The lesion is associated with bothersome appearance · self-reported Fitzpatrick phototype II · the palm is involved · the patient notes the lesion is raised or bumpy · the photograph was taken at an angle · reported duration is less than one week · the contributor is a female aged 50–59.
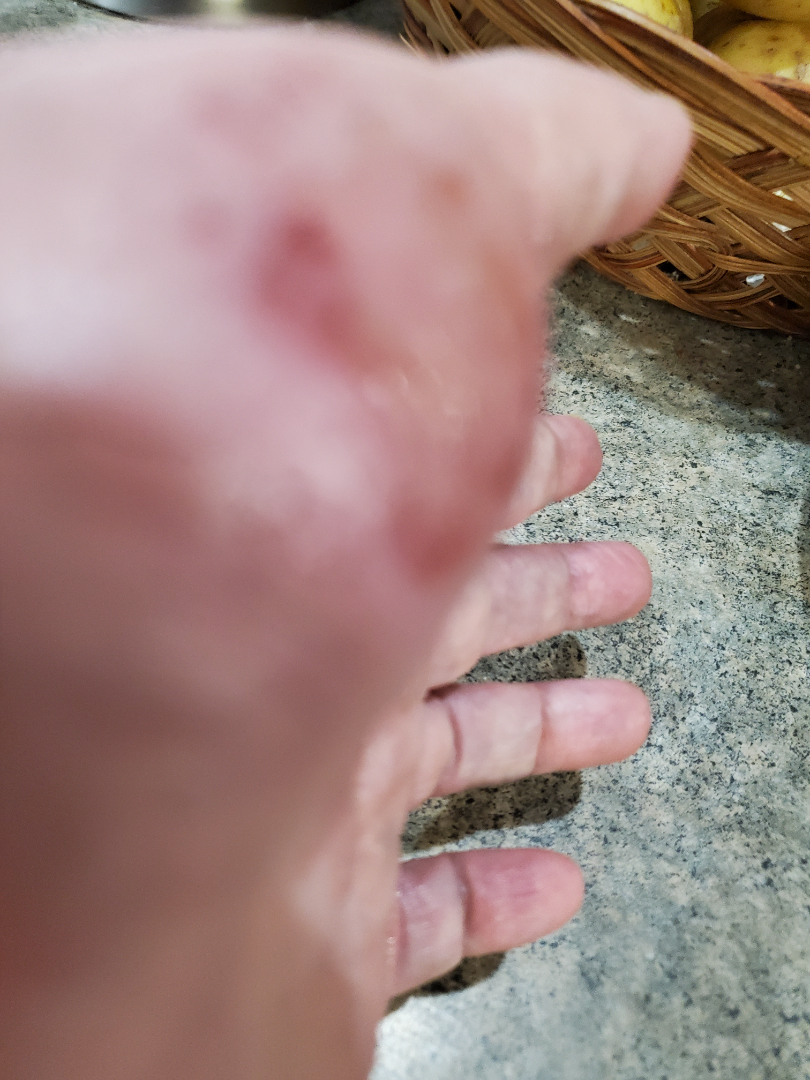{"differential": {"tied_lead": ["Eczema", "Psoriasis"], "unlikely": ["Tinea"]}}